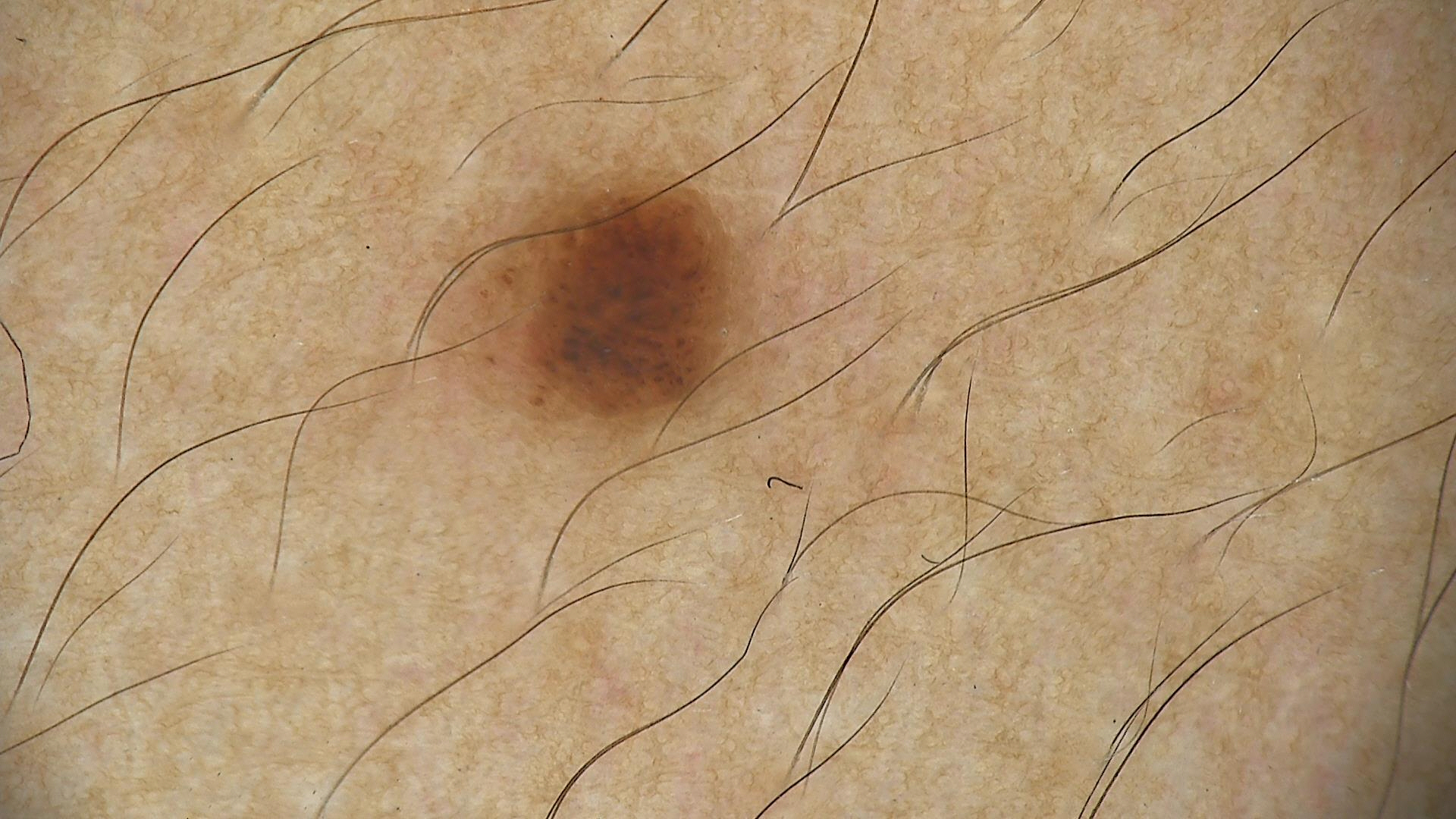modality: dermatoscopy
label: junctional nevus (expert consensus)